A clinical photograph of a skin lesion; a male patient in their 40s; the chart notes prior skin cancer (patient or family), pesticide exposure, no tobacco use, and no alcohol use; skin type II.
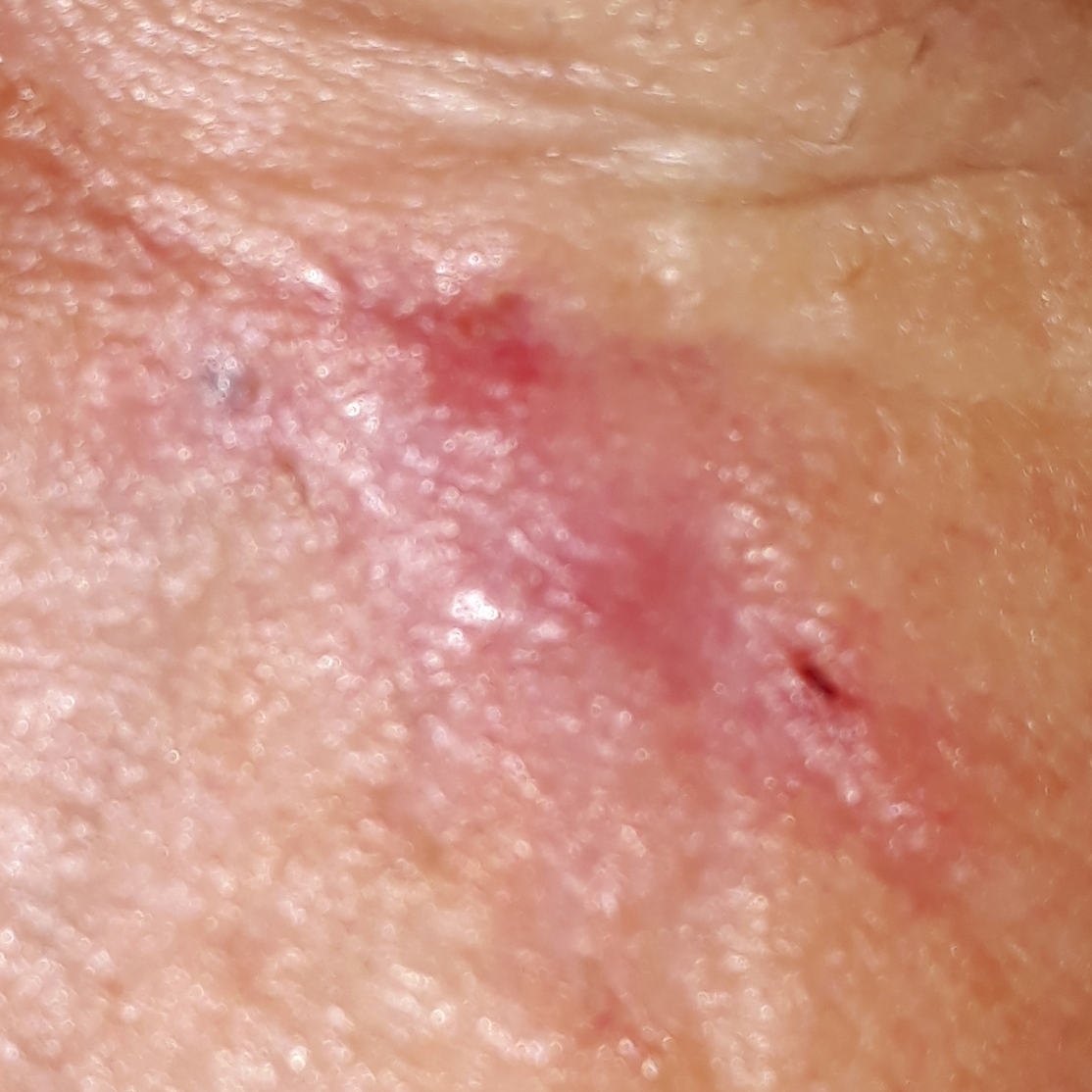Summary:
The lesion was found on the face.
Diagnosis:
Histopathologically confirmed as a basal cell carcinoma.